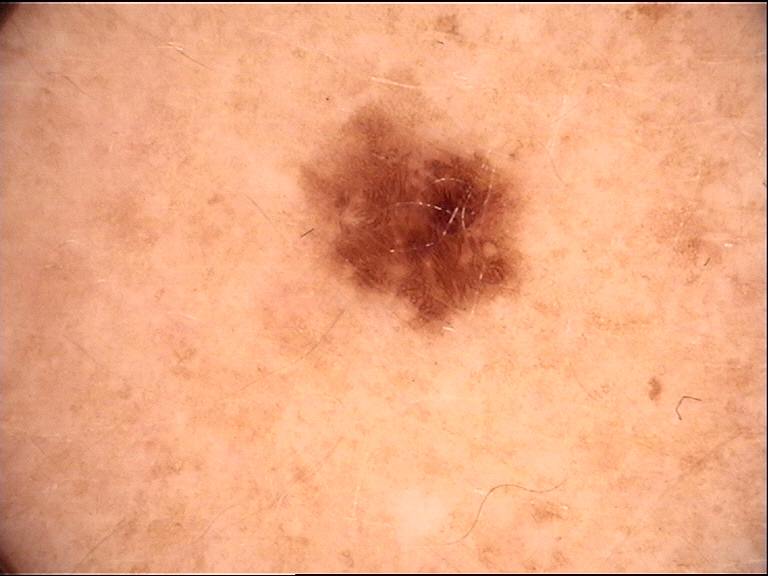Case:
– assessment: dysplastic junctional nevus (expert consensus)